A dermoscopic close-up of a skin lesion.
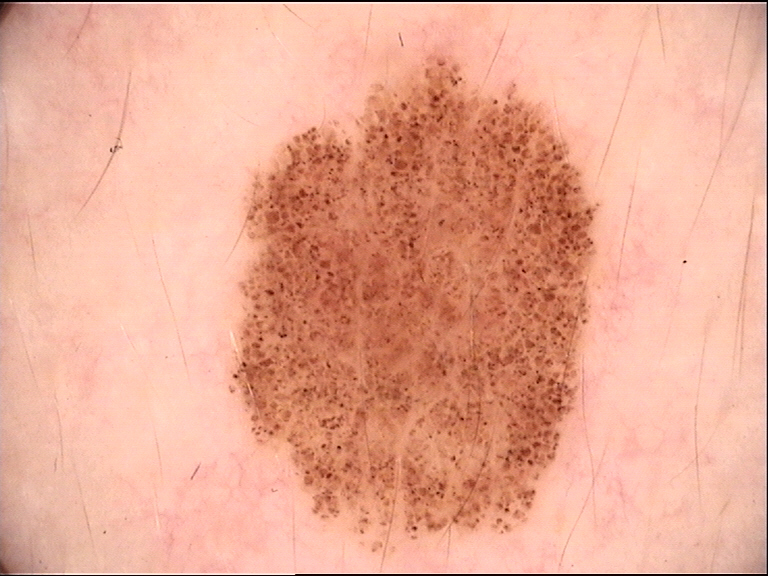Consistent with a dysplastic junctional nevus.